A dermoscopic image of a skin lesion: 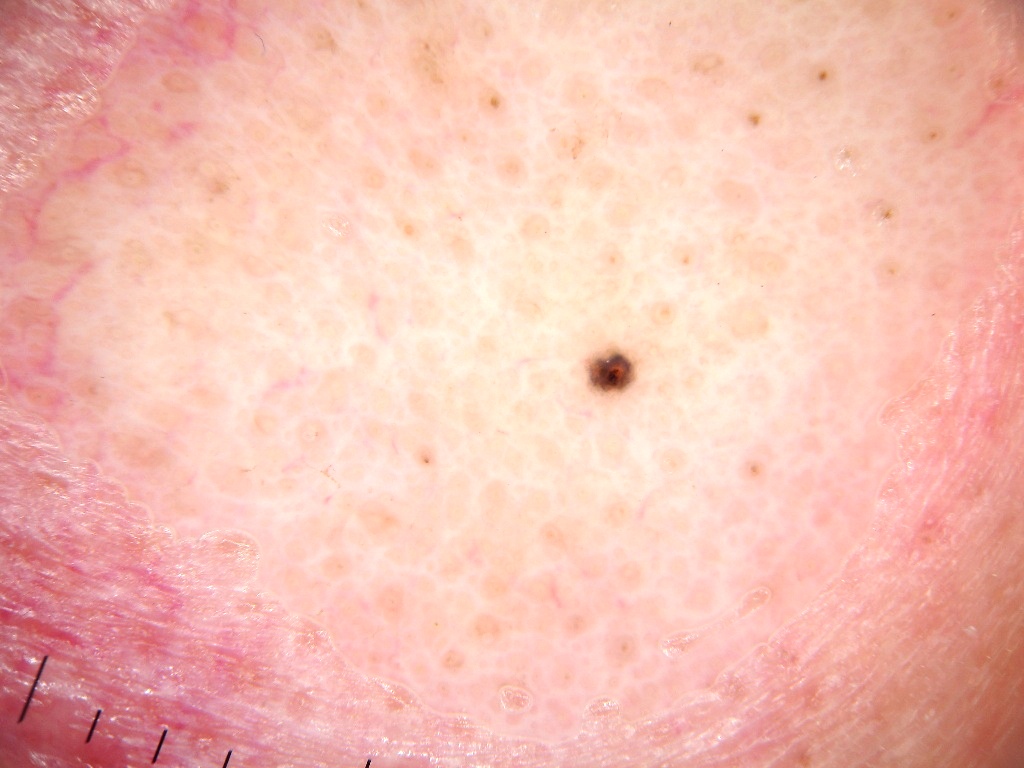lesion size = small | absent dermoscopic findings = streaks and globules | lesion location = 584 345 637 397 | diagnosis = a benign lesion.